A dermoscopic photograph of a skin lesion.
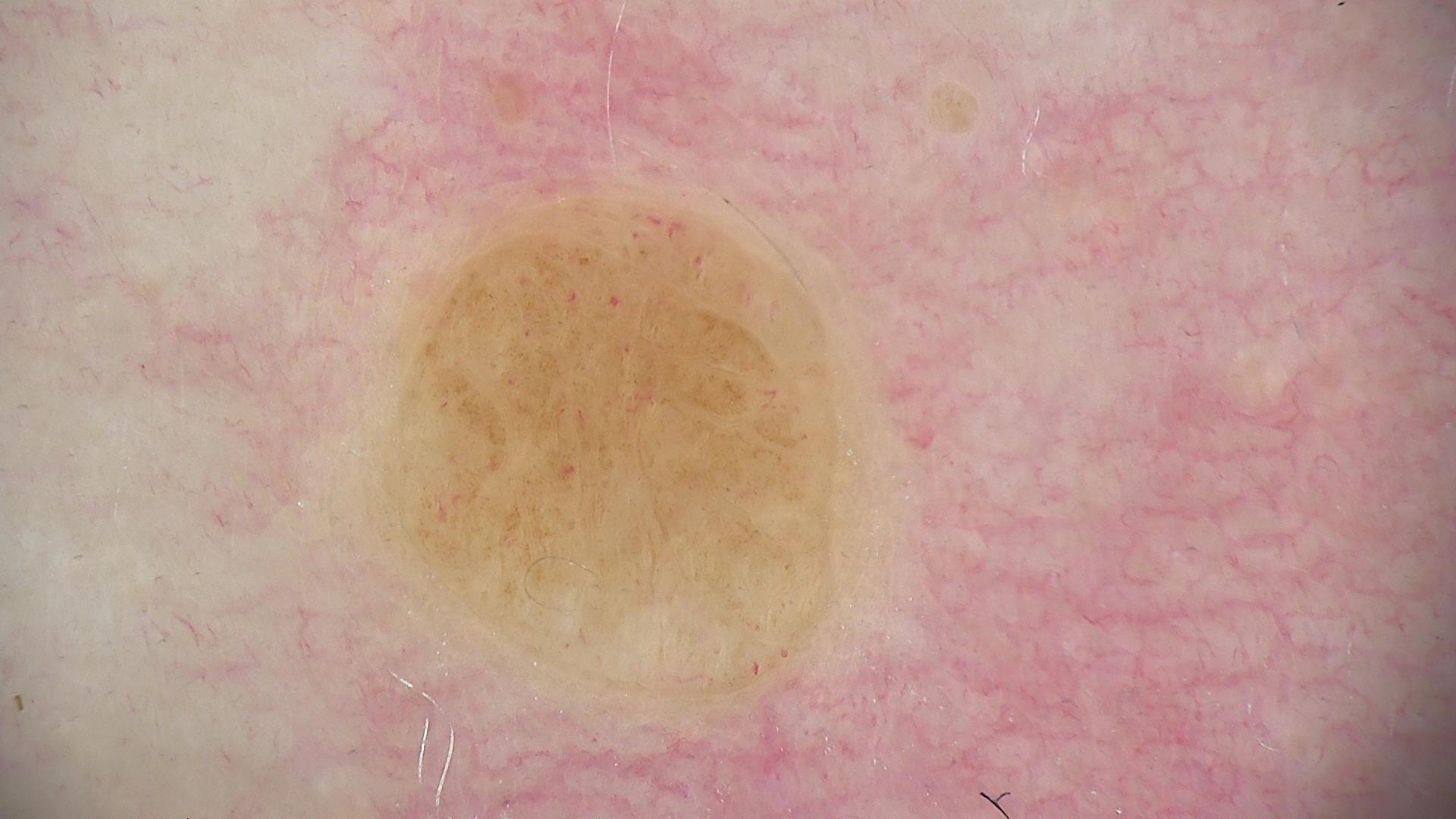Q: What is this lesion?
A: dermal nevus (expert consensus)